The photograph is a close-up of the affected area; the arm is involved; the subject is a female aged 18–29 — 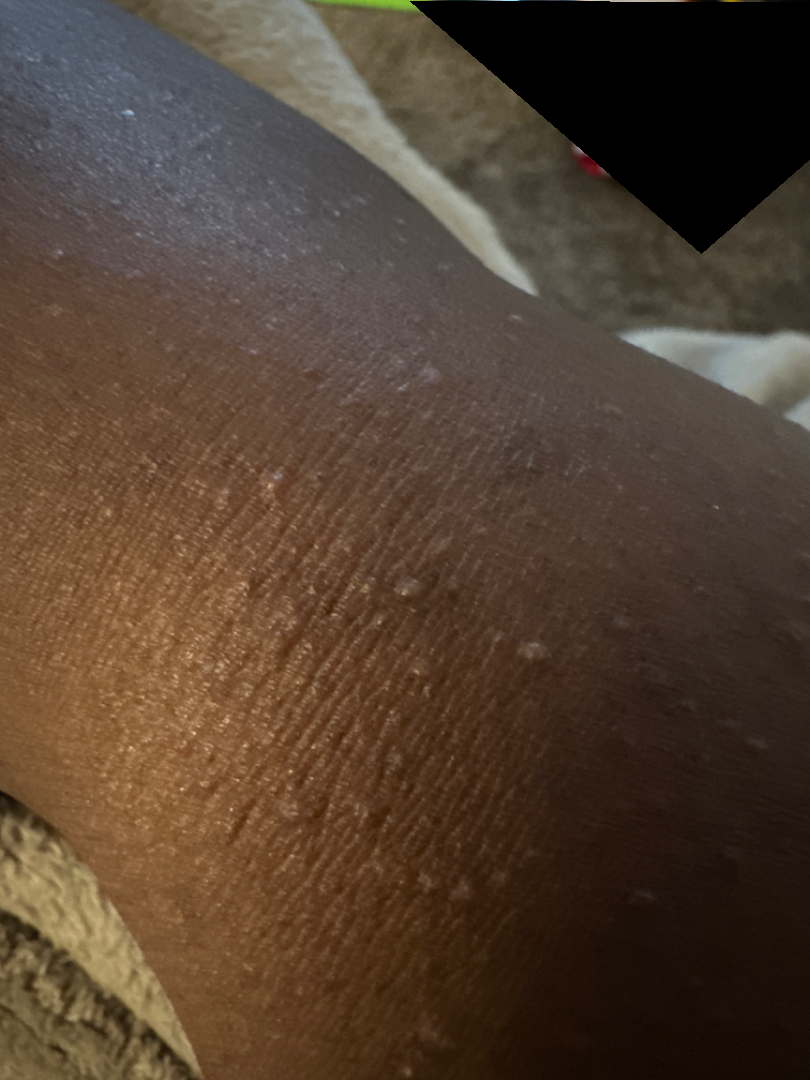present for — one to four weeks
systemic symptoms — none reported
lesion texture — fluid-filled
reported symptoms — itching, enlargement, bothersome appearance and burning
patient's own categorization — a rash
assessment — Eczema (weight 0.35); Lichen nitidus (weight 0.35); Milia (weight 0.15); Hypersensitivity (weight 0.15)